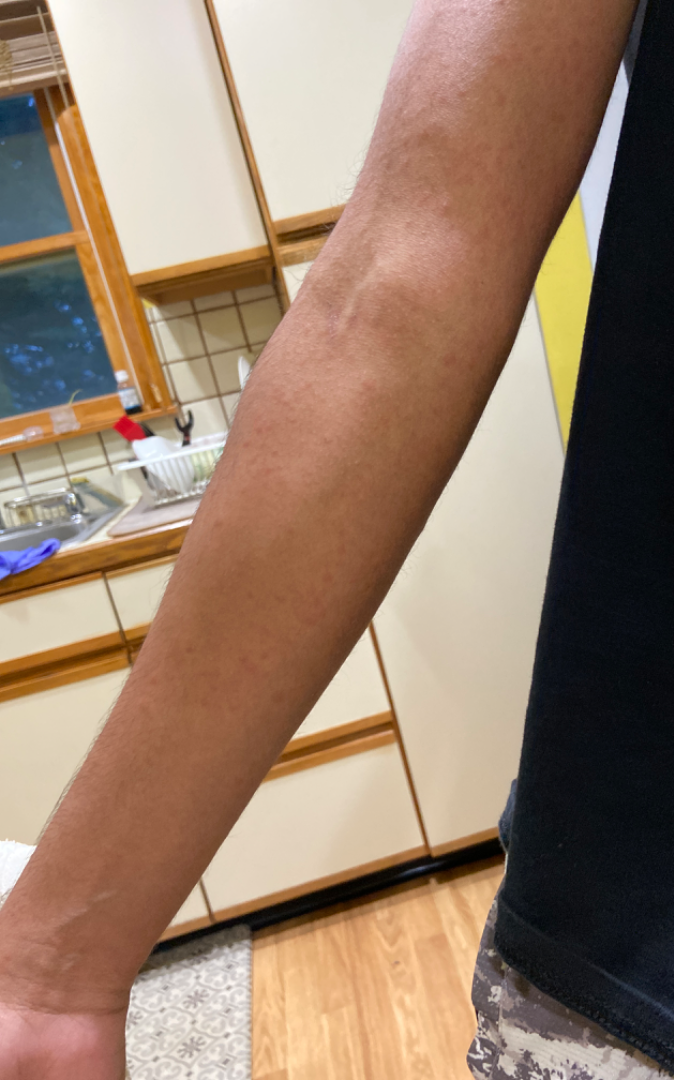No differential diagnosis could be assigned on photographic review. The patient did not report lesion symptoms. The photograph was taken at a distance. The leg, arm and head or neck are involved. No associated systemic symptoms reported. Male subject, age 18–29. The patient considered this a rash. Reported duration is one to four weeks. The patient notes the lesion is raised or bumpy.